Texture is reported as flat · the arm is involved · the patient considered this a rash · the patient reported no systemic symptoms · skin tone: non-clinician graders estimated a Monk Skin Tone of 1 · this image was taken at an angle.
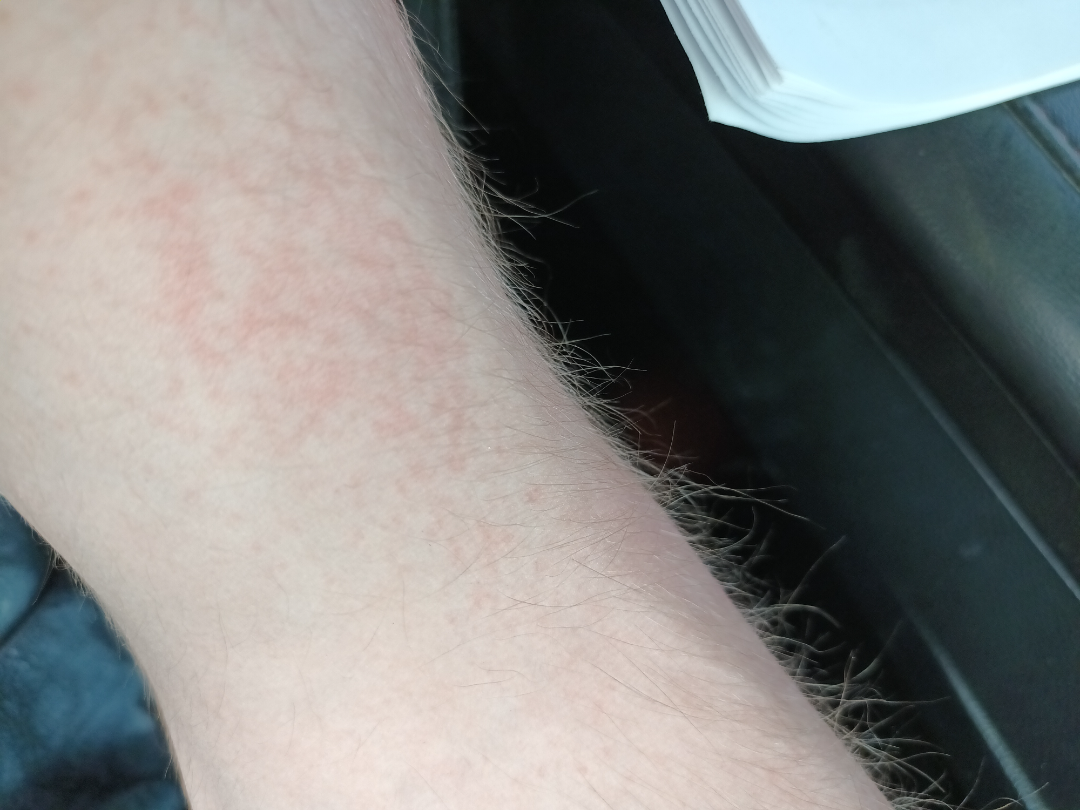assessment: indeterminate